A patient 24 years of age: 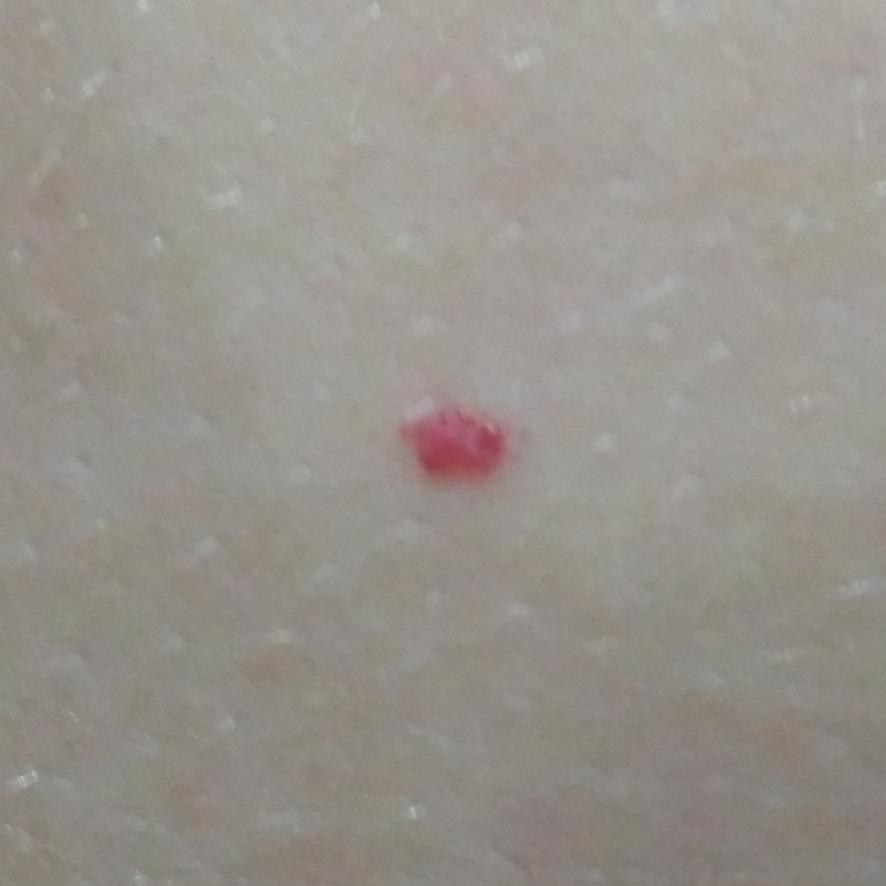The lesion was found on the chest. Diagnosed by dermatologist consensus as a benign lesion — a nevus.